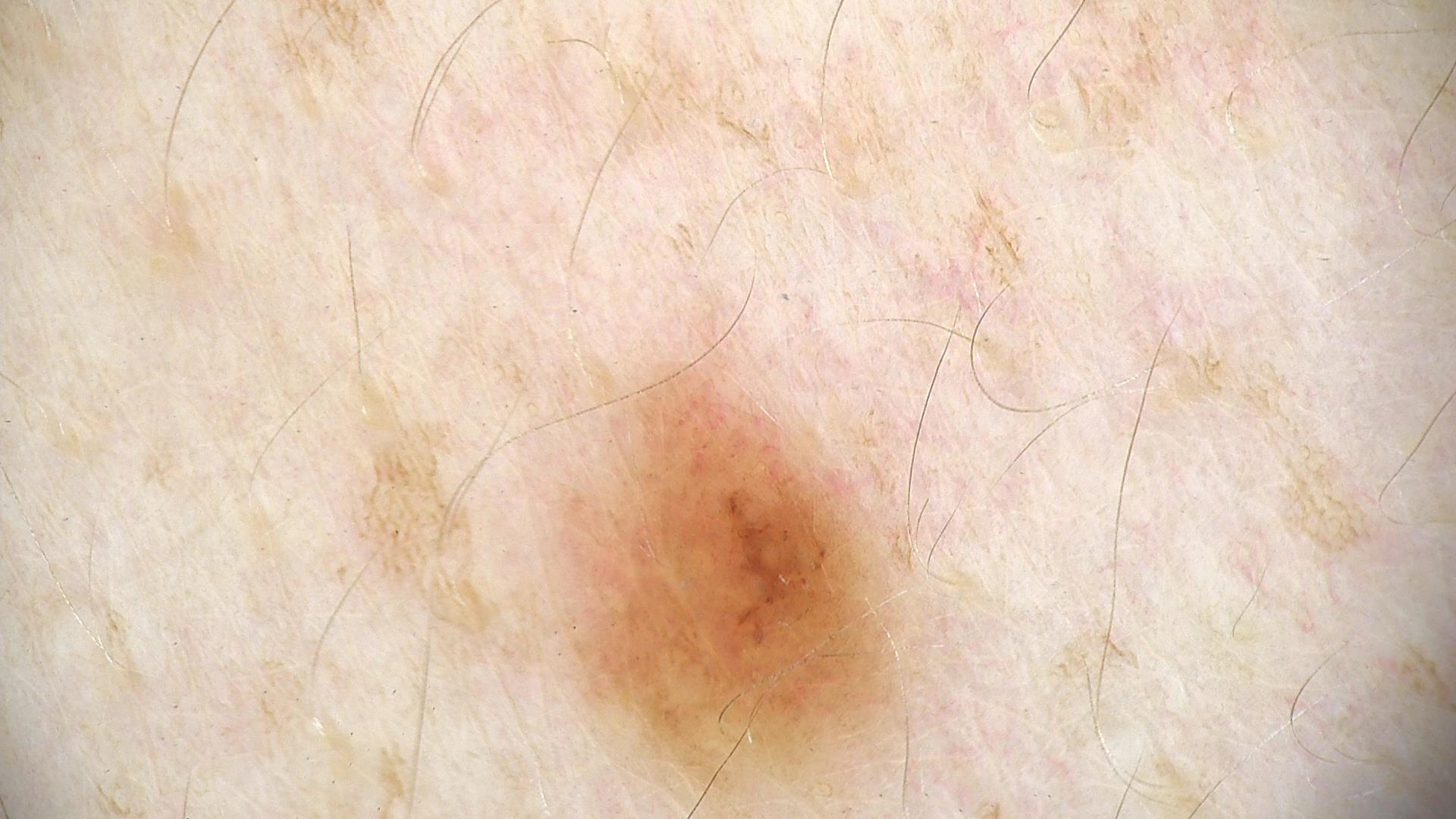Q: What is the diagnosis?
A: dysplastic junctional nevus (expert consensus)